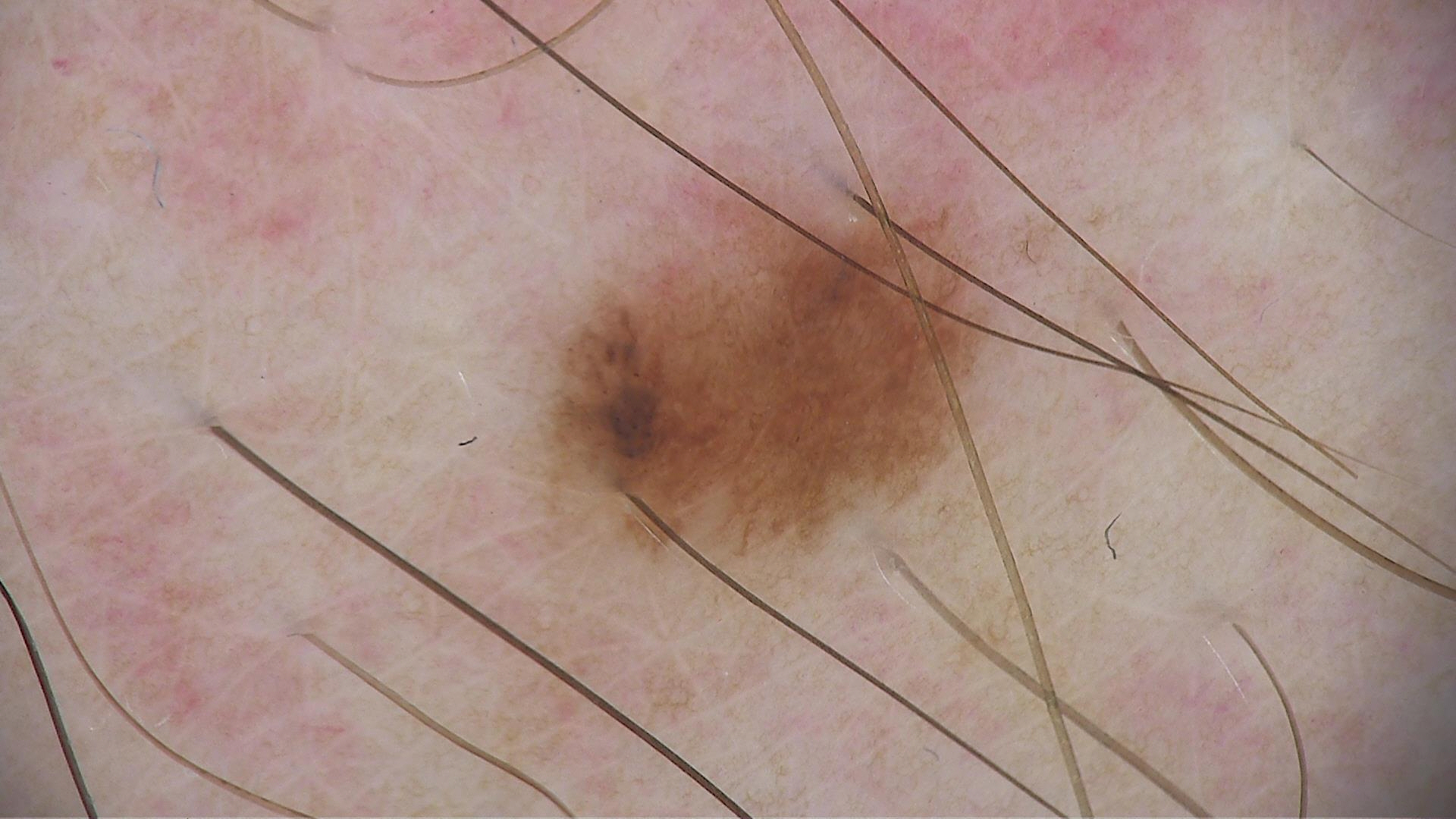Diagnosed as a dysplastic junctional nevus.